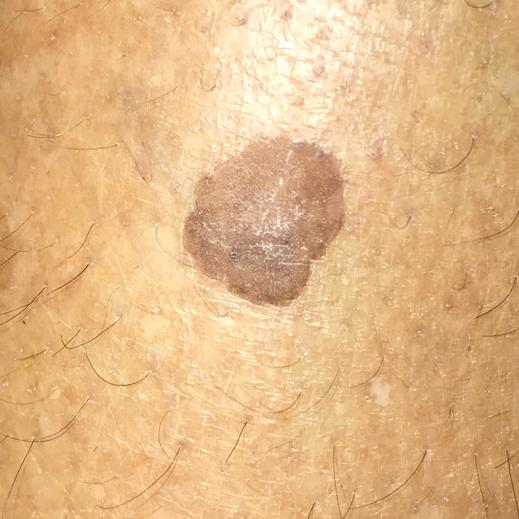{"patient": {"age": 57}, "lesion_location": "a thigh", "symptoms": {"present": ["growth", "elevation"]}, "diagnosis": {"name": "seborrheic keratosis", "code": "SEK", "malignancy": "benign", "confirmation": "clinical consensus"}}